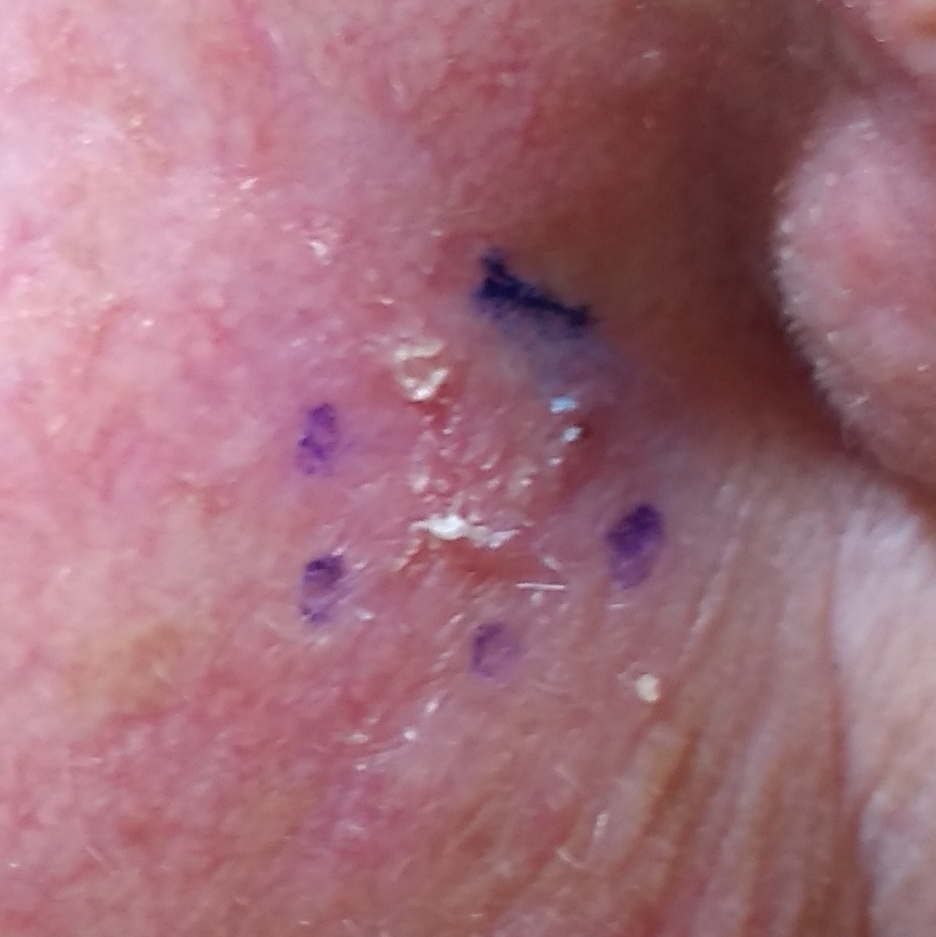Findings: A female patient aged 74. A clinical photograph of a skin lesion. The lesion measures approximately 10 × 8 mm. Pathology: On biopsy, the diagnosis was an actinic keratosis.